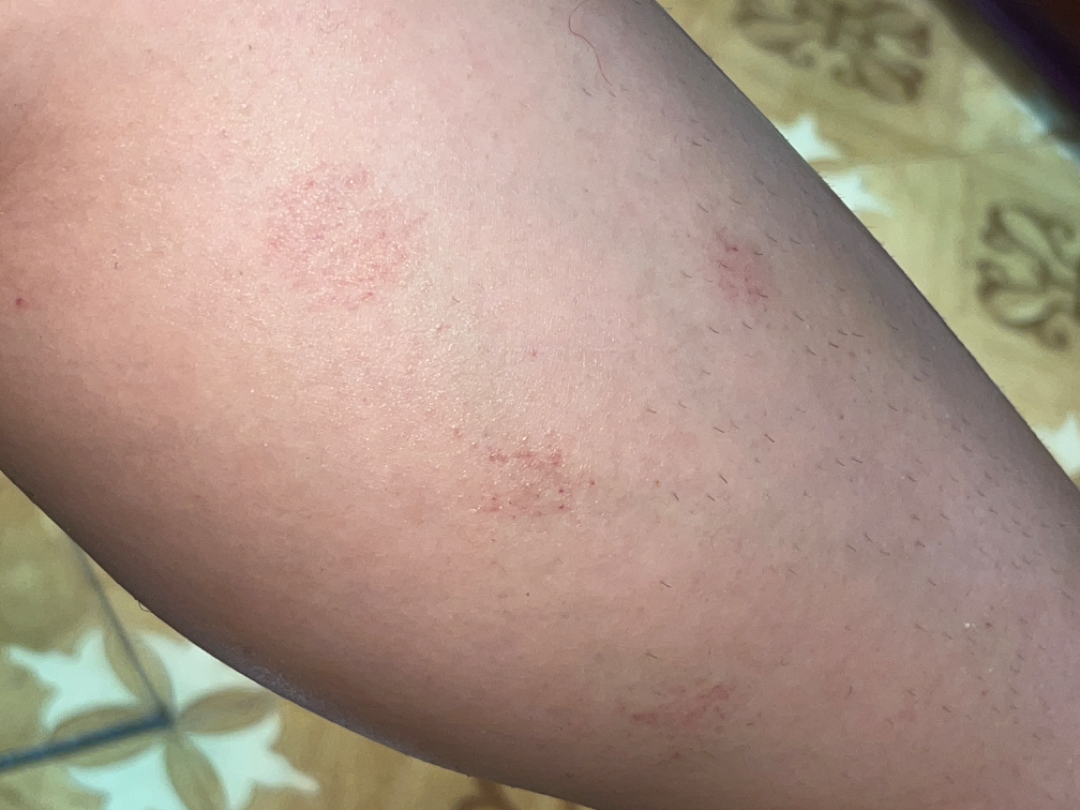On independent review by the dermatologists, Eczema (primary); Pigmented purpuric eruption (less likely).